A dermoscopic view of a skin lesion · a male subject roughly 30 years of age — 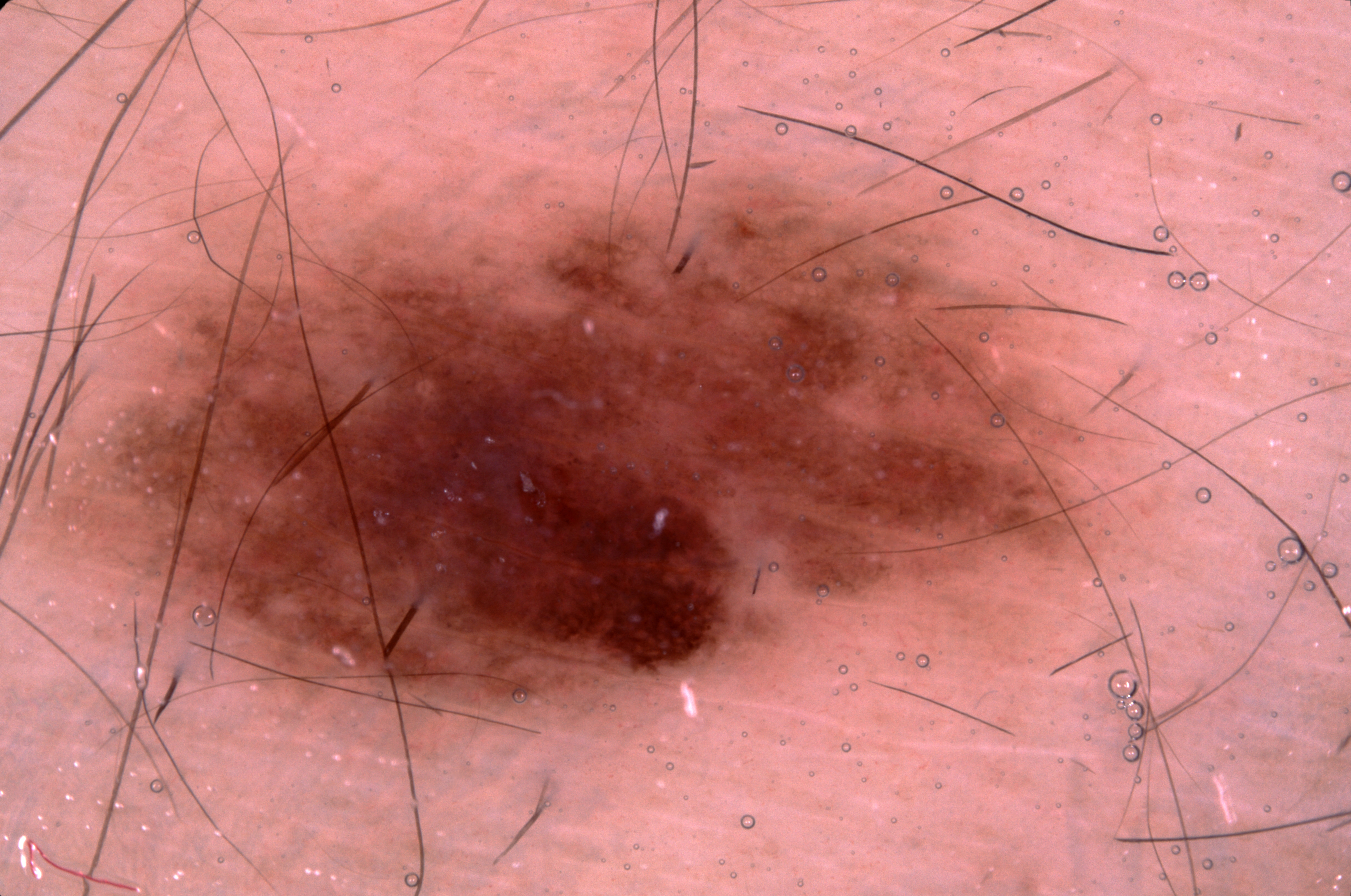Case summary:
- features · pigment network
- size · ~41% of the field
- bounding box · x1=46 y1=147 x2=1143 y2=743
- impression · a melanocytic nevus